A clinical photograph showing a skin lesion. A male patient in their early 80s — 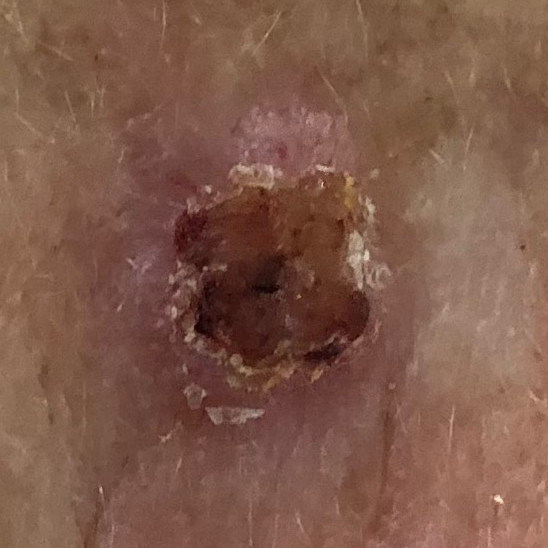  lesion_location: the face
  lesion_size:
    diameter_1_mm: 6.0
    diameter_2_mm: 5.0
  symptoms:
    present:
      - pain
      - elevation
      - itching
      - bleeding
  diagnosis:
    name: basal cell carcinoma
    code: BCC
    malignancy: malignant
    confirmation: histopathology